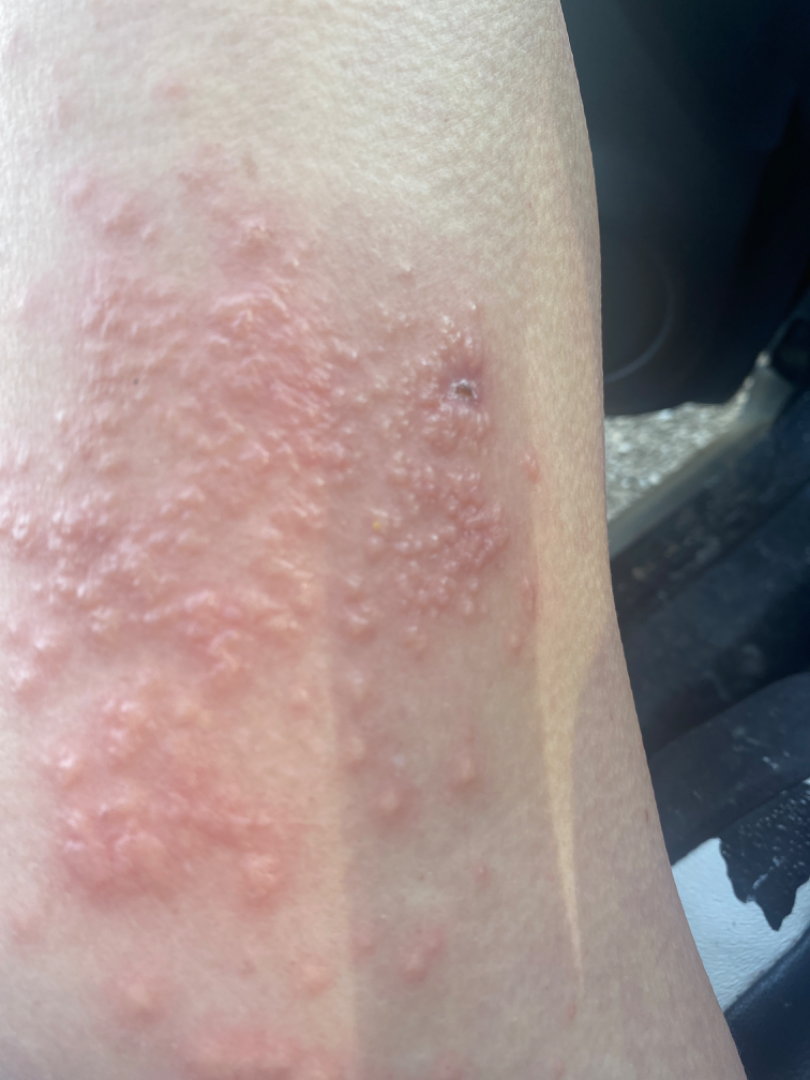Assessment: The case was difficult to assess from the available photograph.